A dermoscopic photograph of a skin lesion: 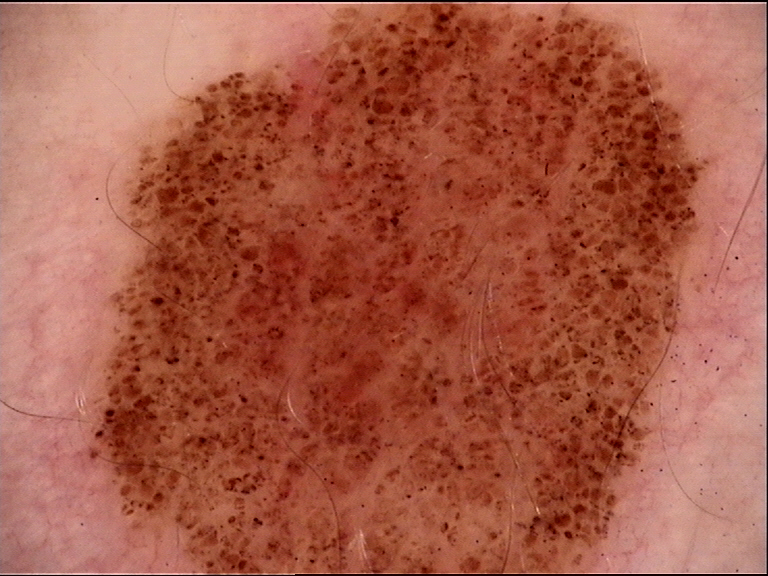Case:
– classification: banal
– label: compound nevus (expert consensus)